A skin lesion imaged with a dermatoscope: 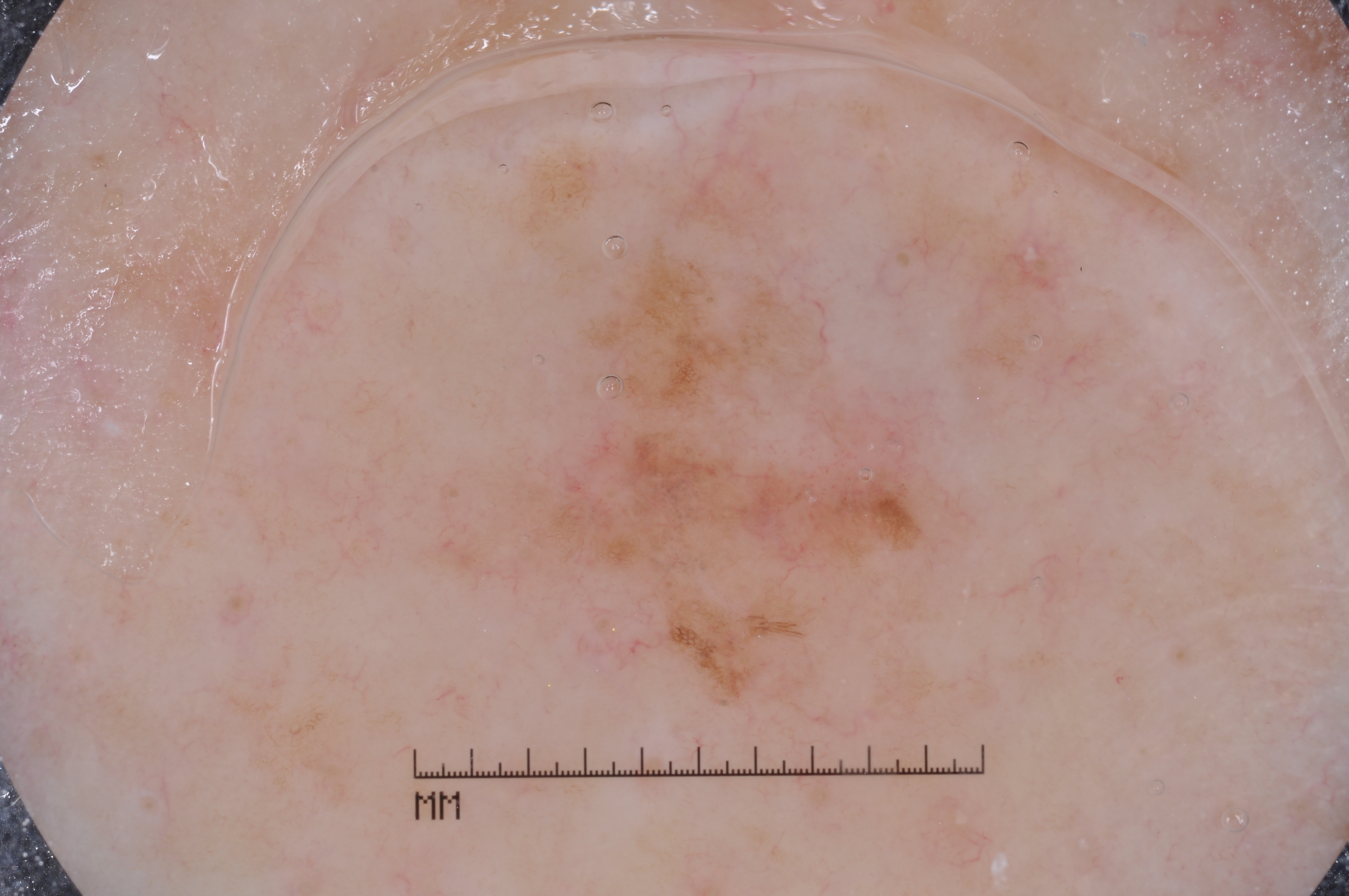Dermoscopic review identifies pigment network. The lesion spans left=426, top=151, right=976, bottom=726. The lesion takes up about 11% of the image. On biopsy, the diagnosis was a melanoma, a malignant skin lesion.